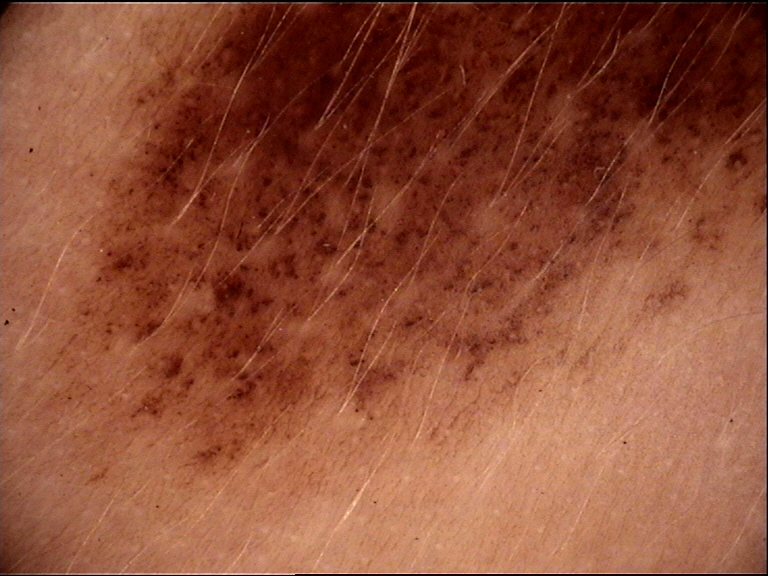image = dermatoscopy | diagnosis = congenital compound nevus (expert consensus).